A skin lesion imaged with a dermatoscope.
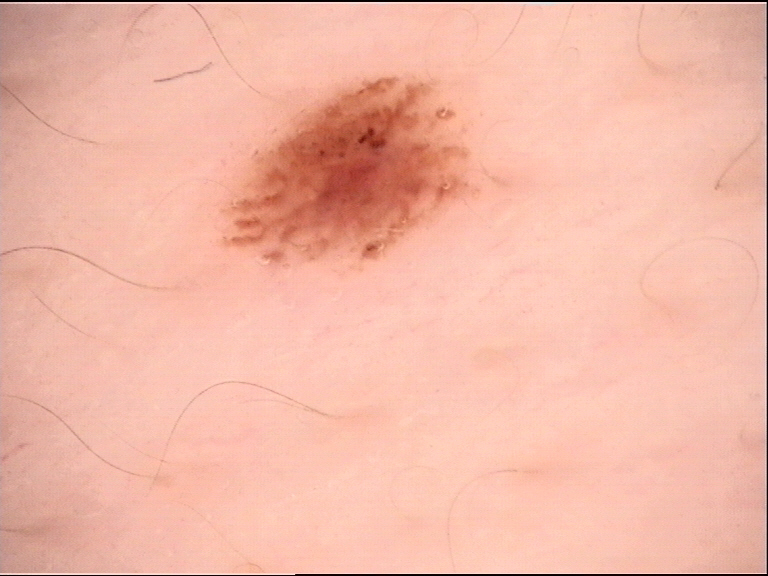label = dysplastic junctional nevus (expert consensus).